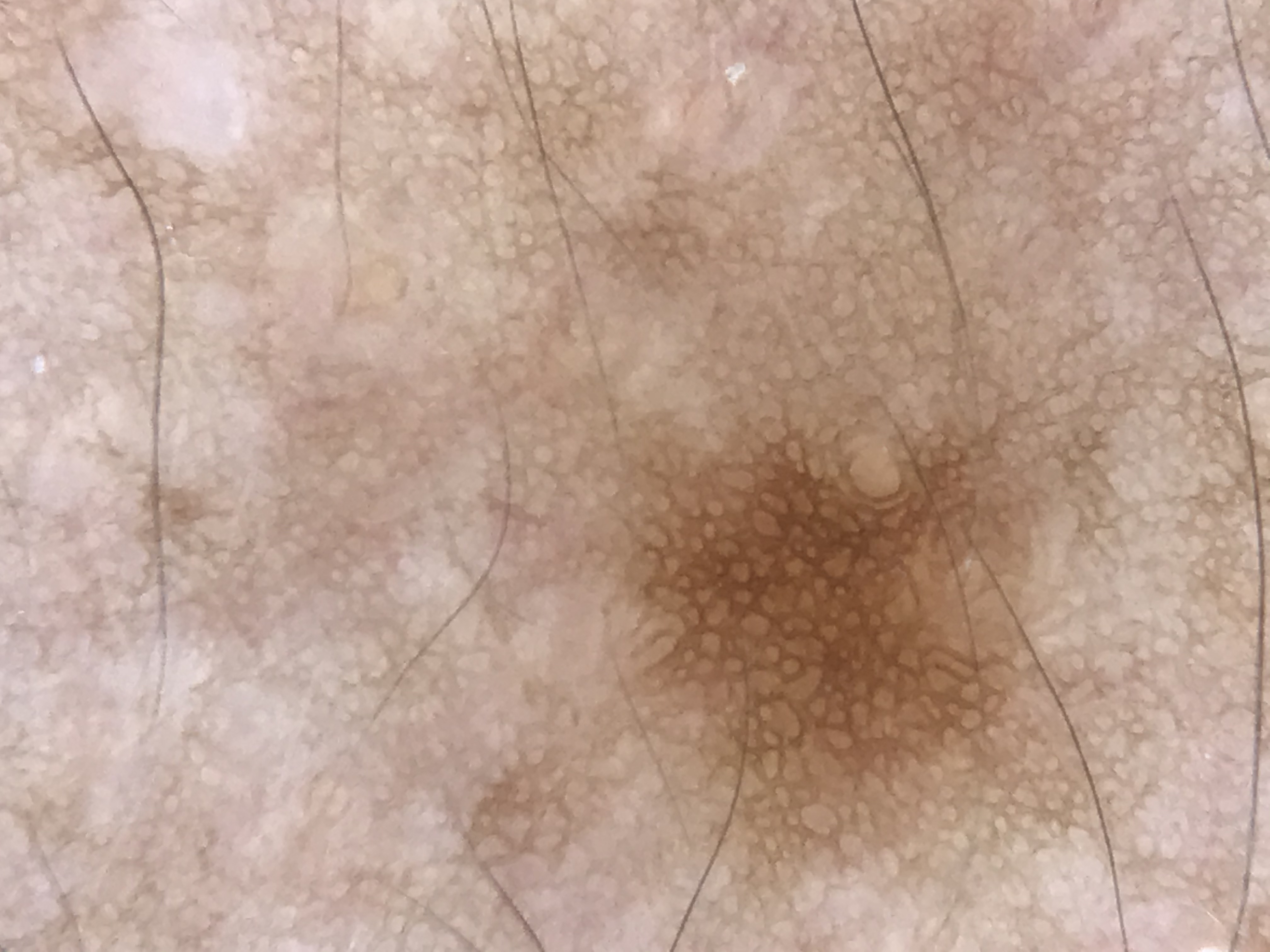image type=dermatoscopy | assessment=solar lentigo (expert consensus).